A dermoscopic close-up of a skin lesion:
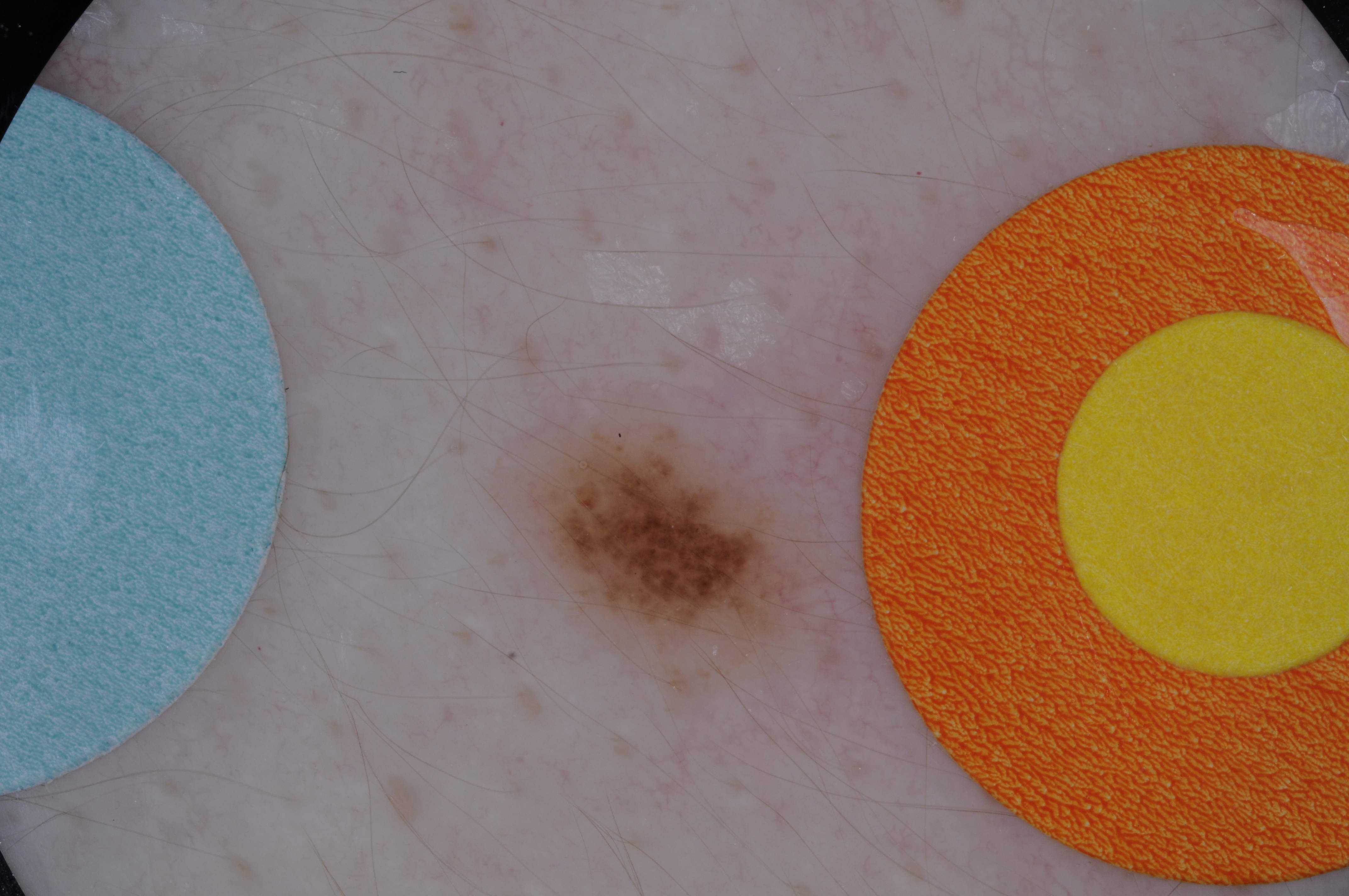Q: What is the lesion's bounding box?
A: [515,417,821,695]
Q: What is this lesion?
A: a benign lesion